A dermoscopy image of a skin lesion; the patient describes having numerous moles; the patient says their skin reddens painfully with sun exposure; on a questionnaire the patient reported immunosuppression, a family history of skin cancer, and a personal history of skin cancer; a male subject aged 65; acquired for a research image collection, with no referral diagnosis: 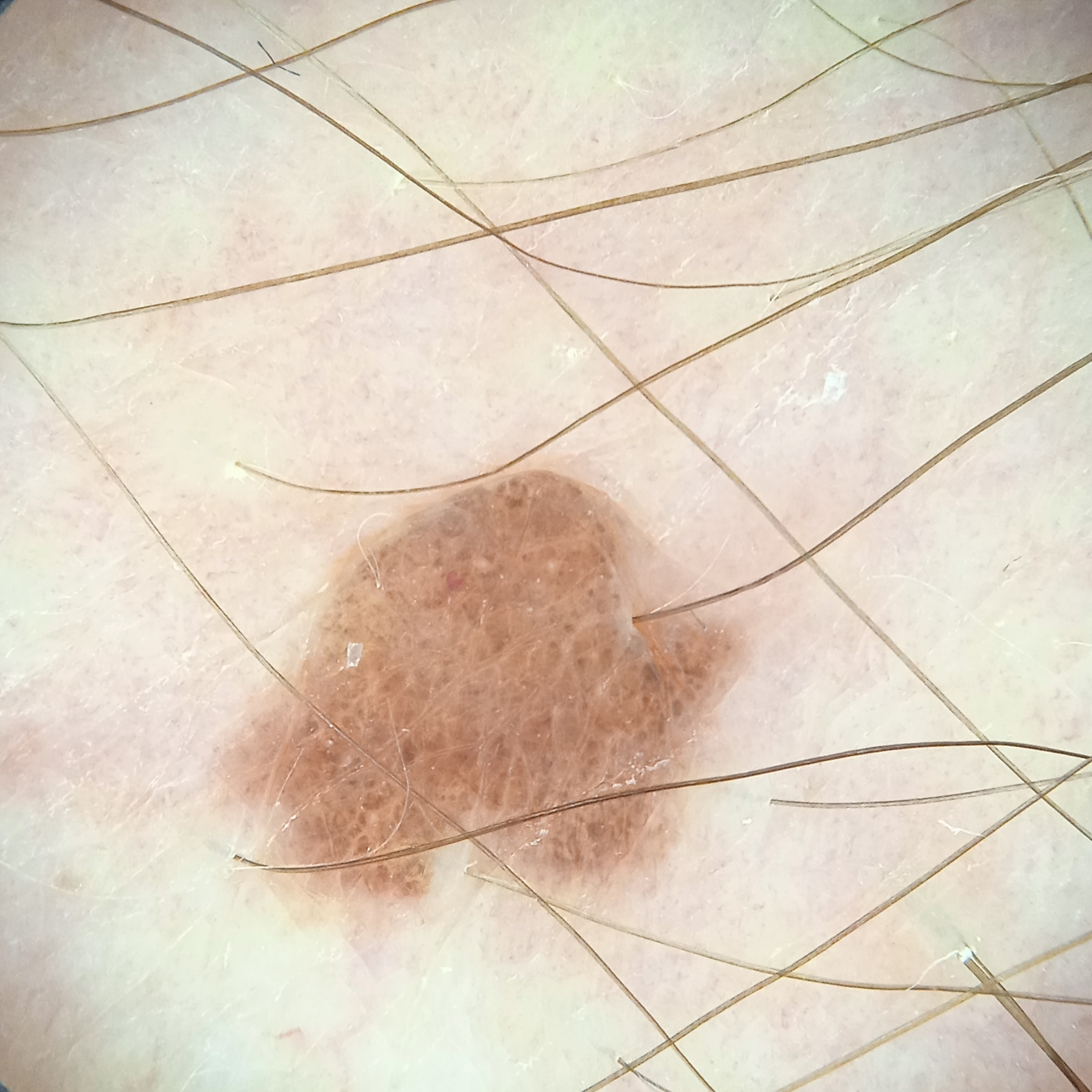– body site — an arm
– lesion size — 5.5 mm
– diagnosis — melanocytic nevus (dermatologist consensus)